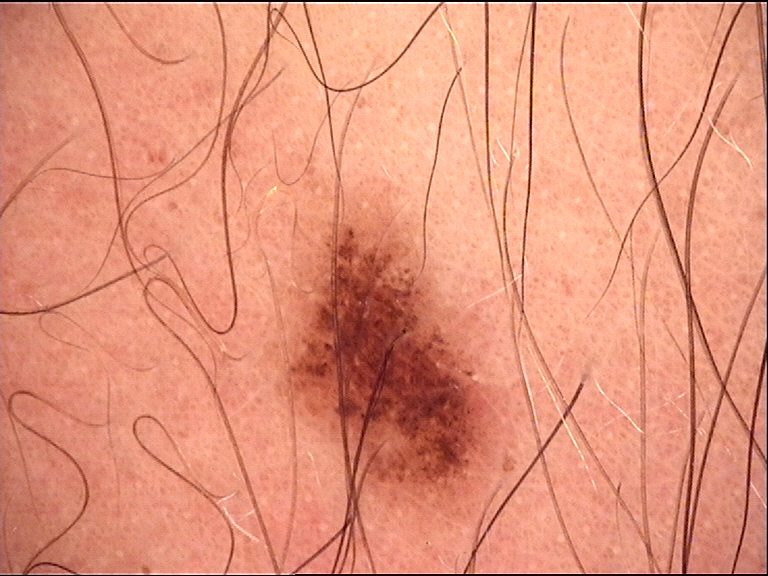diagnostic label: junctional nevus (expert consensus).